A dermoscopic close-up of a skin lesion:
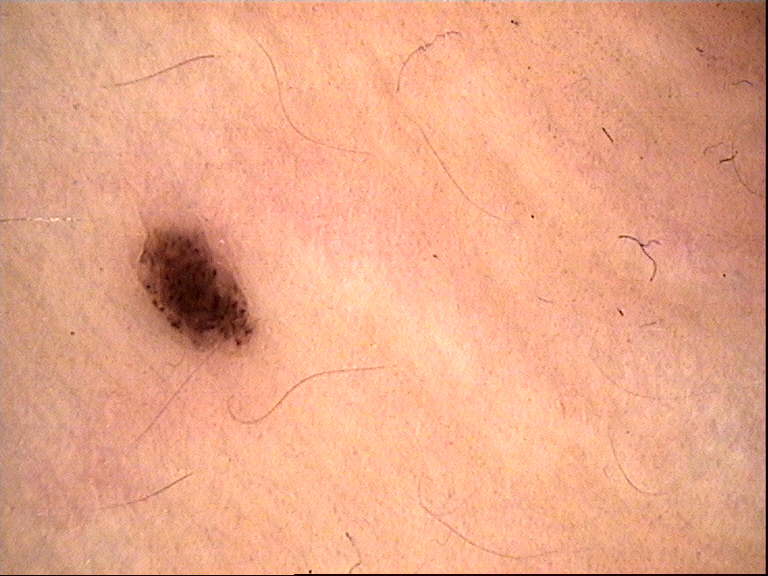Consistent with a benign lesion — a dysplastic compound nevus.